A dermoscopic photograph of a skin lesion:
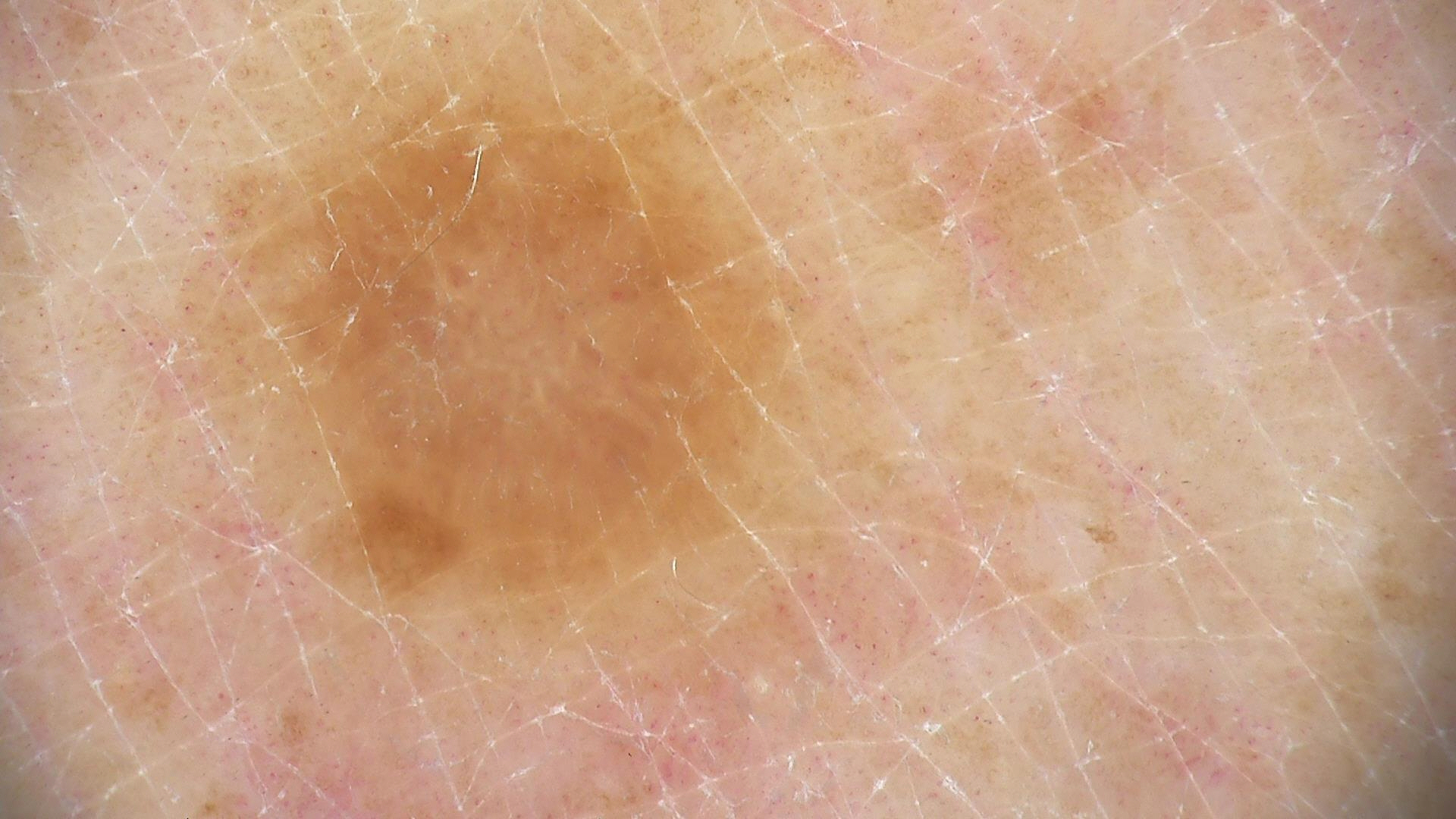assessment = dermatofibroma (expert consensus).